The chart records no first-degree relative with melanoma and no previous melanoma; a contact-polarized dermoscopy image of a skin lesion; a female subject aged around 30:
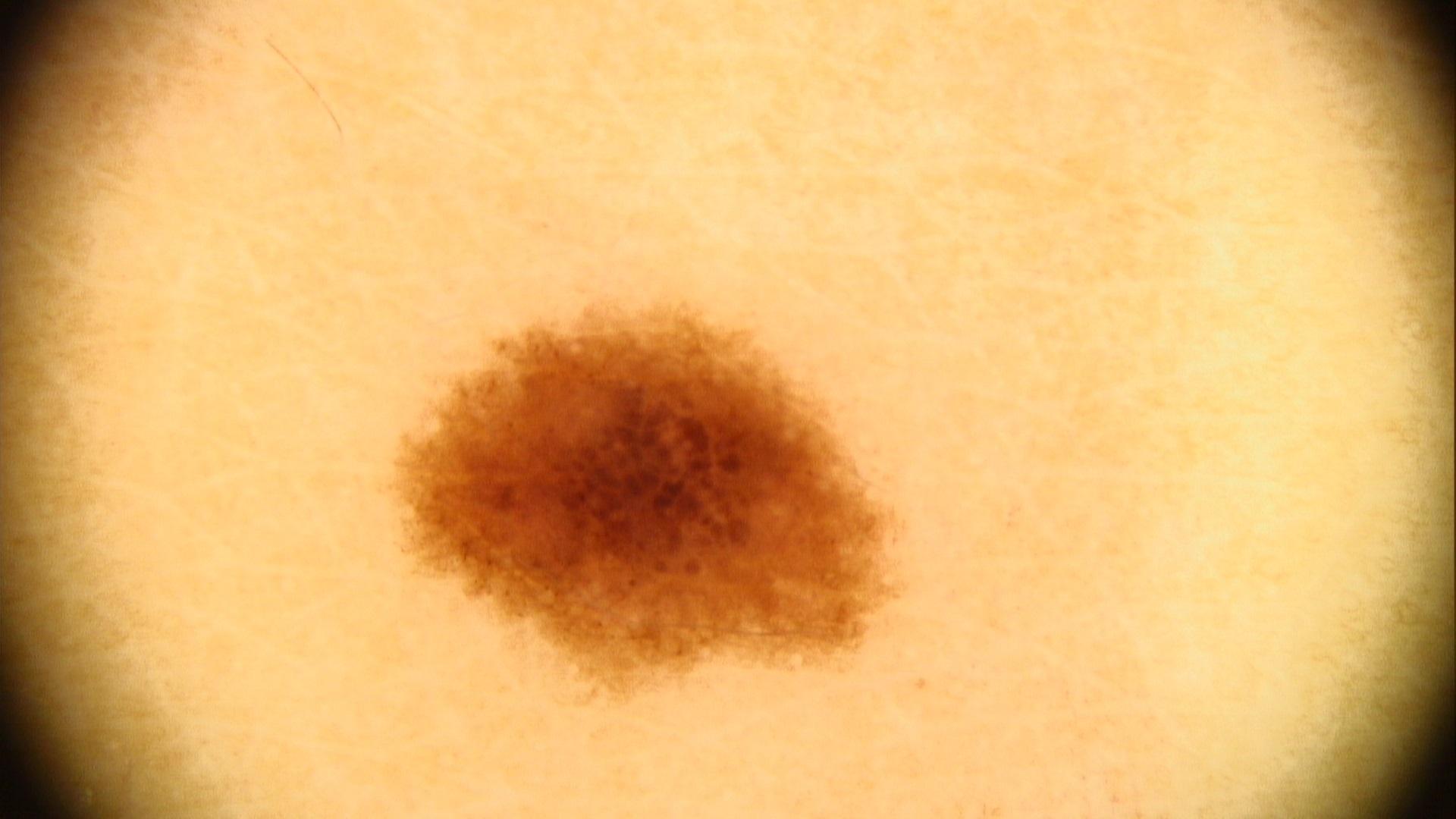The lesion involves the trunk. Consistent with a benign lesion — a nevus.